A dermatoscopic image of a skin lesion.
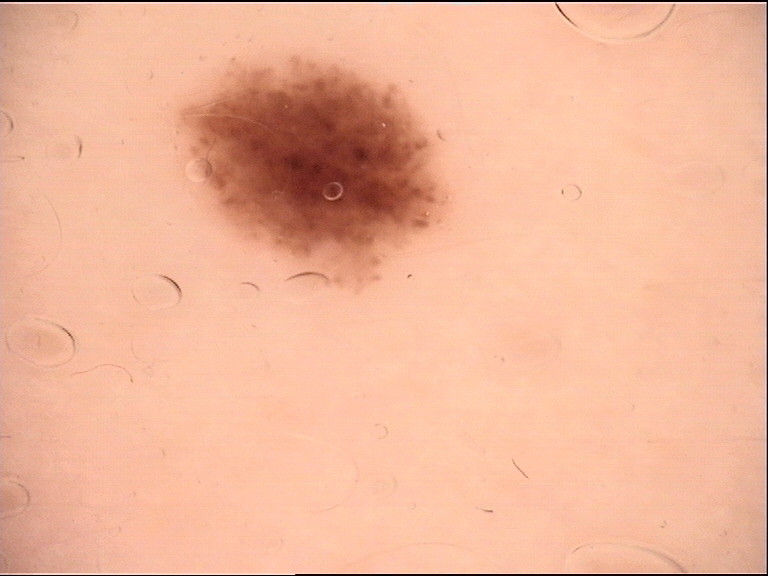diagnosis = dysplastic junctional nevus (expert consensus).